The patient is 18–29, female · the patient considered this a rash · texture is reported as flat · this image was taken at a distance · reported lesion symptoms include burning and pain · the affected area is the arm · the patient reports the condition has been present for about one day — 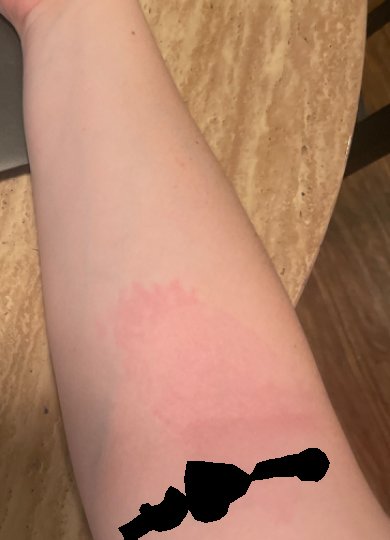On remote review of the image: most consistent with Eczema; with consideration of Allergic Contact Dermatitis.